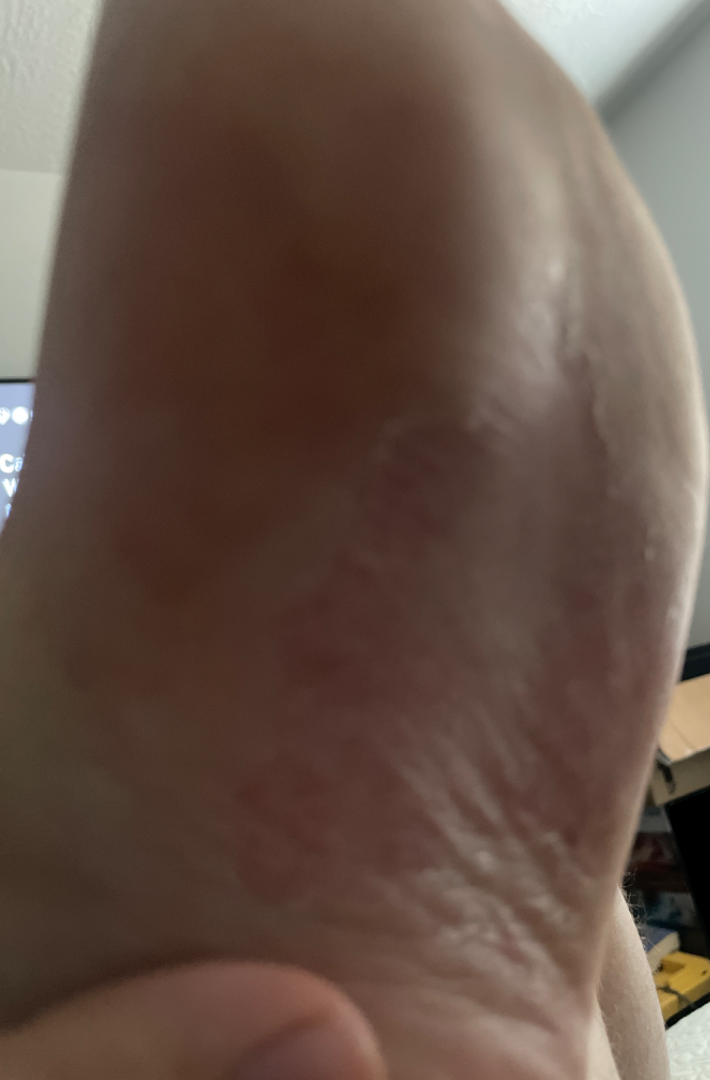Notes:
* assessment: indeterminate from the photograph